The photograph is a close-up of the affected area: 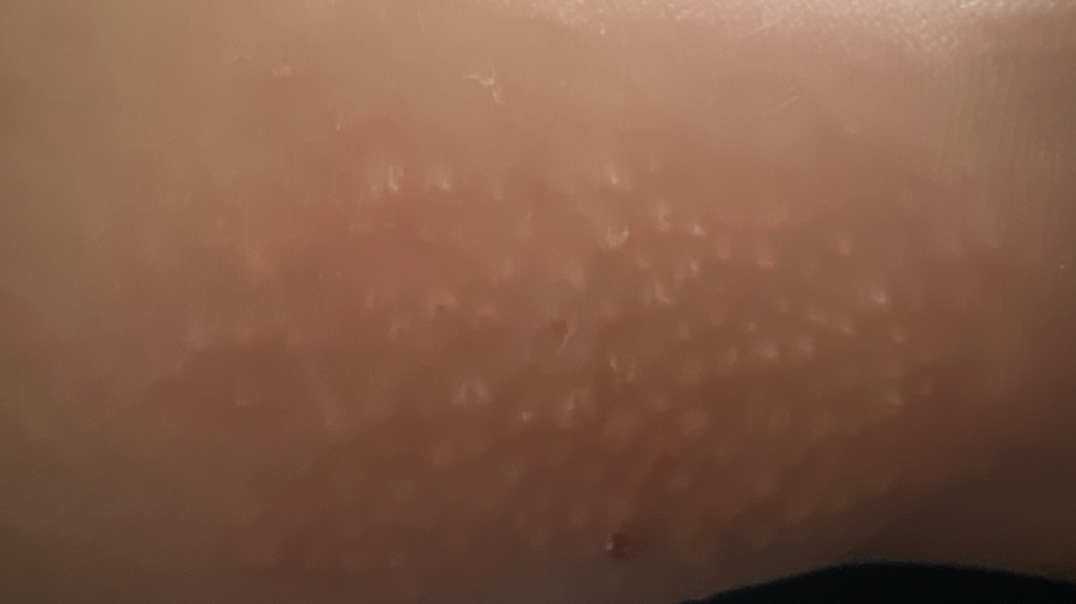The dermatologist could not determine a likely condition from the photograph alone.